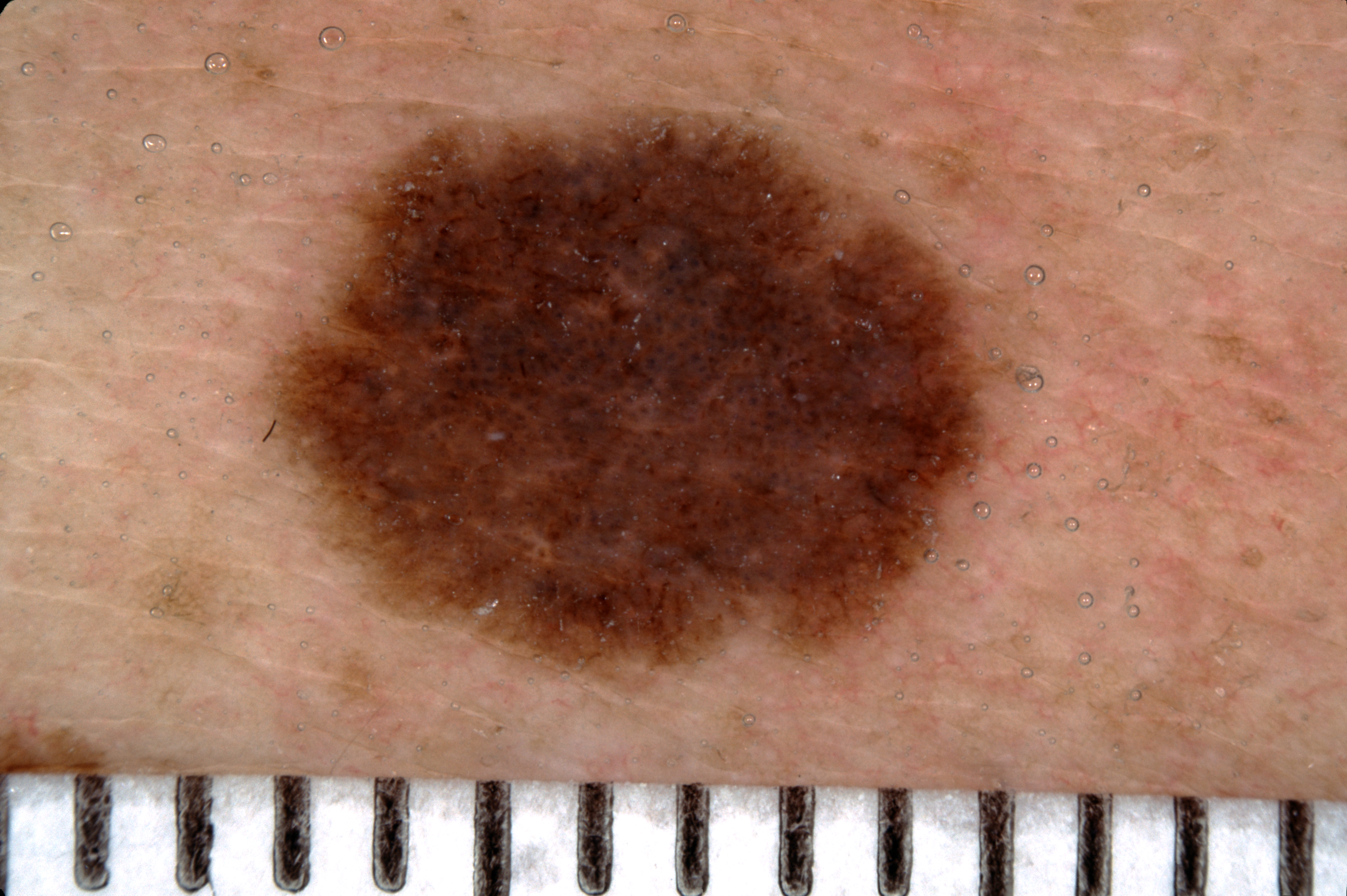A dermoscopic image of a skin lesion. A male subject, aged approximately 35. A mid-sized lesion within the field. On dermoscopy, the lesion shows negative network and pigment network, with no milia-like cysts or streaks. With coordinates (x1, y1, x2, y2), the lesion is located at [259, 101, 1015, 693]. Expert review diagnosed this as a melanocytic nevus.